A skin lesion imaged with a dermatoscope · a male patient 62 years old · few moles overall by the patient's own estimate · on a questionnaire the patient reported no prior organ transplant: 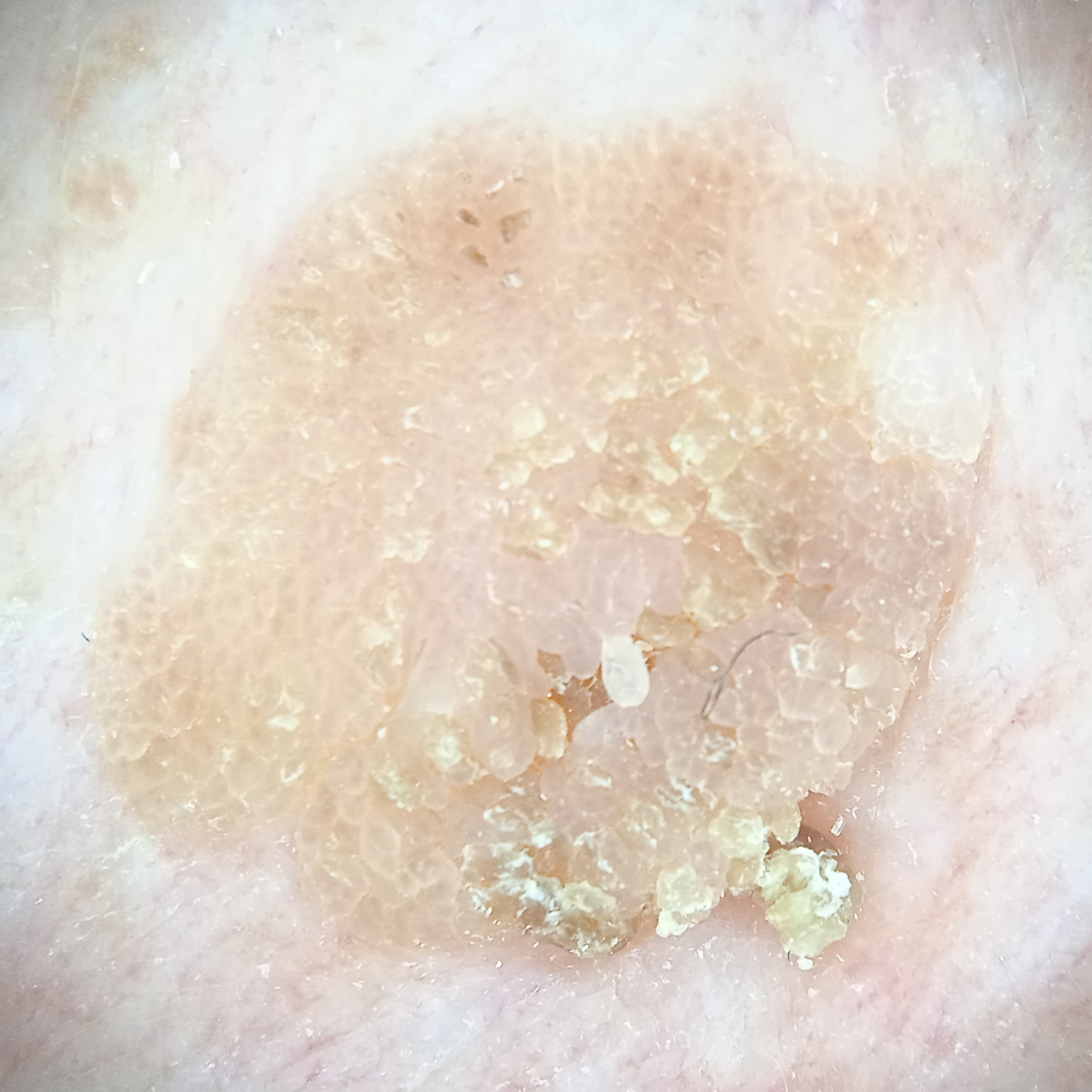{
  "lesion_location": "the torso",
  "lesion_size": {
    "diameter_mm": 11.3
  },
  "diagnosis": {
    "name": "seborrheic keratosis",
    "malignancy": "benign"
  }
}